A male patient about 85 years old or older · a dermoscopic photograph of a skin lesion: 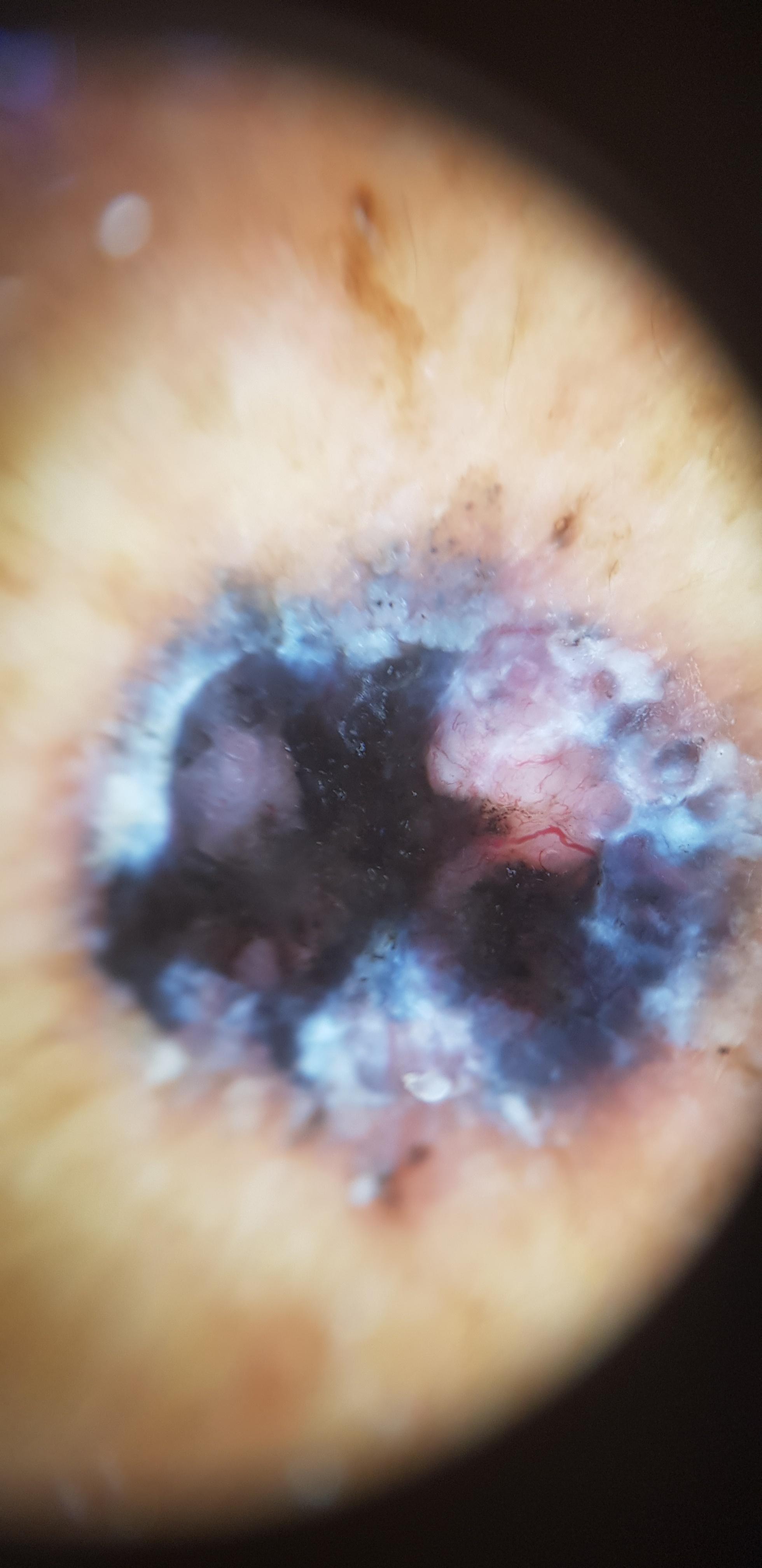Findings: The lesion is located on the posterior trunk. Conclusion: Histopathological examination showed a basal cell carcinoma.